This is a close-up image. The contributor is a male aged 30–39. The head or neck, arm and palm are involved — 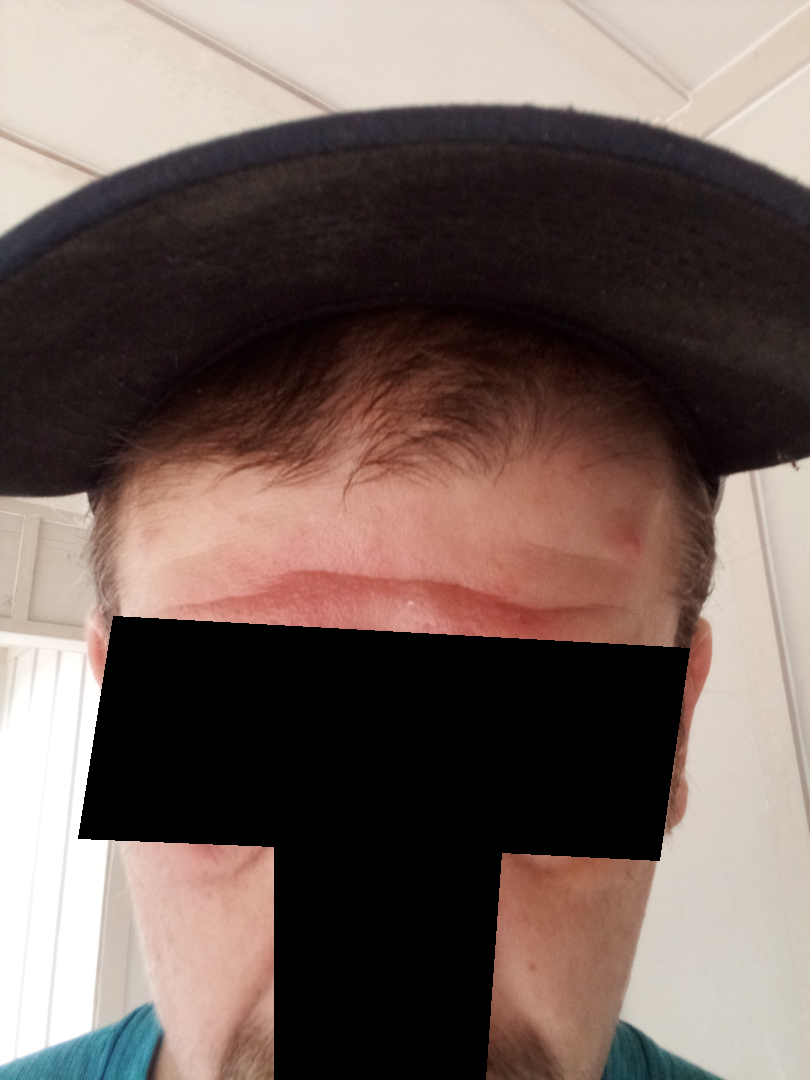{"assessment": "ungradable on photographic review", "duration": "less than one week", "symptoms": ["itching", "burning"], "systemic_symptoms": "none reported", "patient_category": "a rash", "skin_tone": {"fitzpatrick": "II"}, "texture": ["fluid-filled", "raised or bumpy"]}